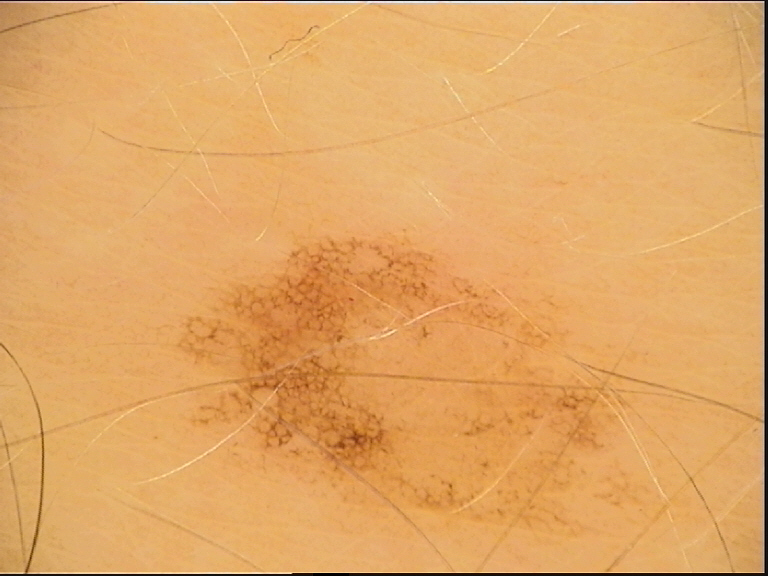A dermoscopic image of a skin lesion. The diagnosis was a dysplastic junctional nevus.